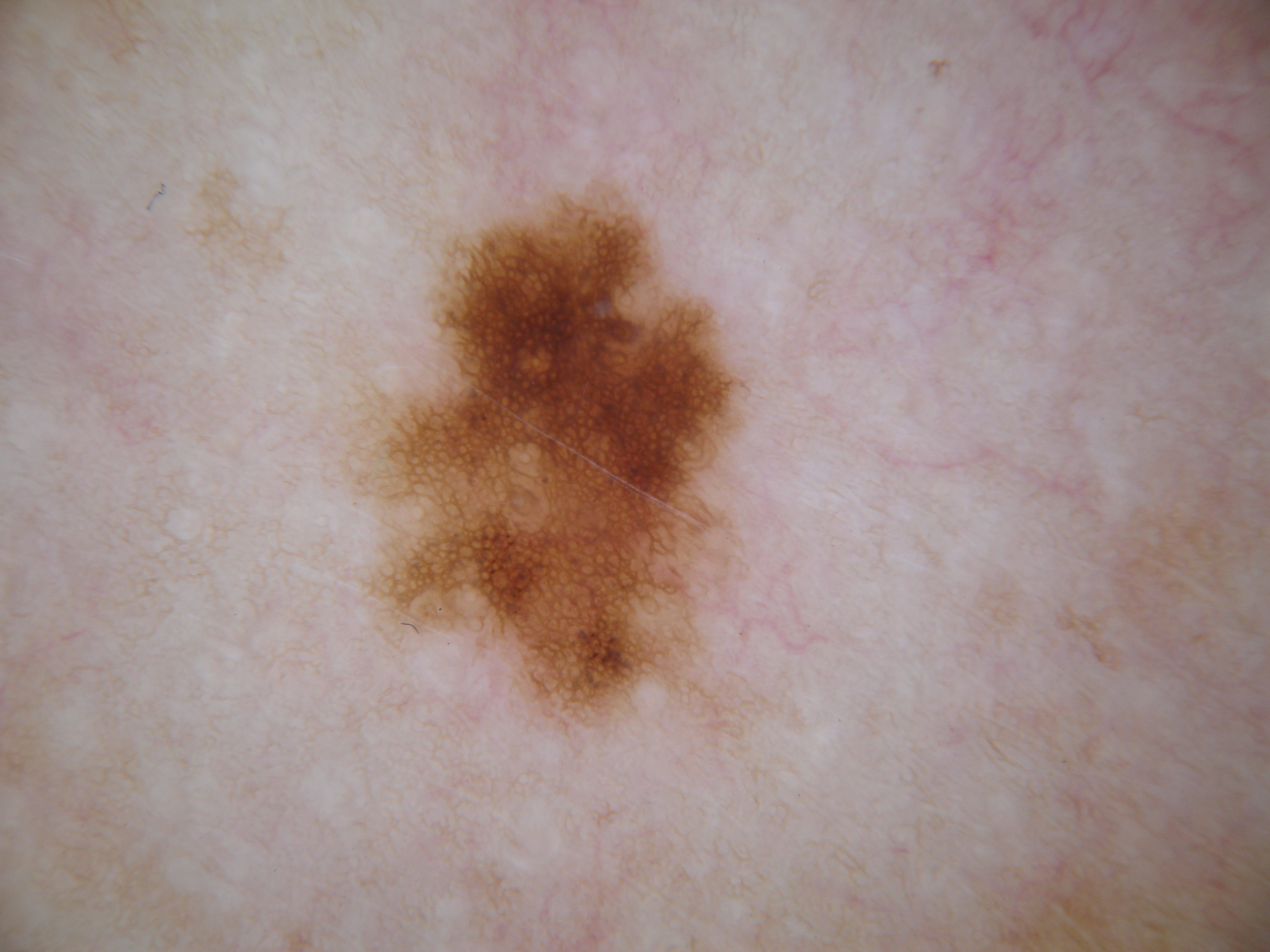image type — dermatoscopic image of a skin lesion; lesion bbox — x1=344 y1=174 x2=770 y2=745; dermoscopic pattern — streaks, pigment network, and globules; assessment — a melanocytic nevus, a benign skin lesion.